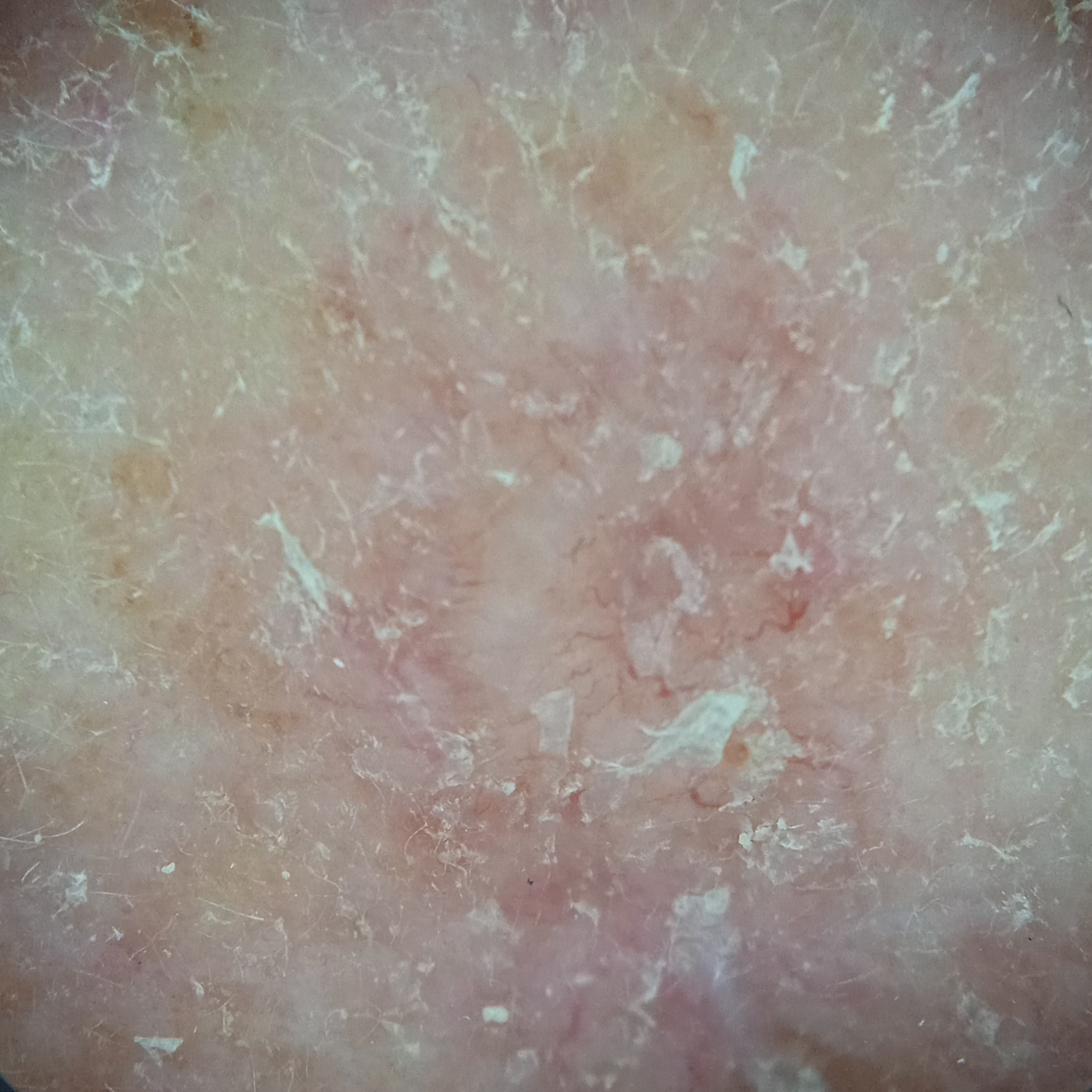<record>
<image>dermoscopic image</image>
<referral>research study (no referral diagnosis)</referral>
<sun_reaction>skin tans without first burning</sun_reaction>
<patient>
<age>92</age>
<sex>female</sex>
</patient>
<risk_factors>
<positive>a personal history of cancer, a family history of skin cancer</positive>
<negative>no sunbed use, no prior organ transplant</negative>
</risk_factors>
<lesion_size>
<diameter_mm>7.0</diameter_mm>
</lesion_size>
<diagnosis>
<name>basal cell carcinoma</name>
<malignancy>malignant</malignancy>
</diagnosis>
</record>